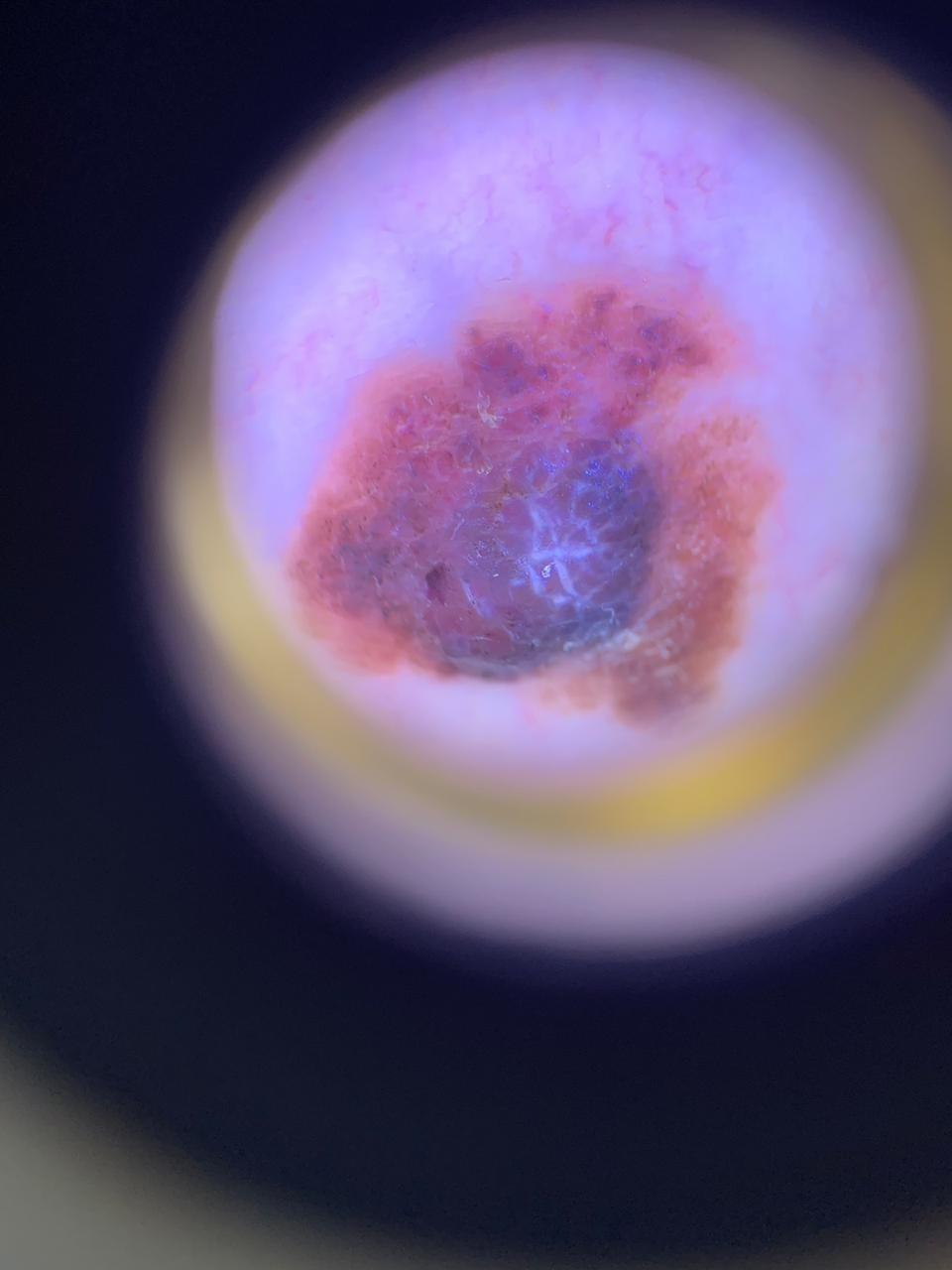Confirmed on histopathology as a melanoma.